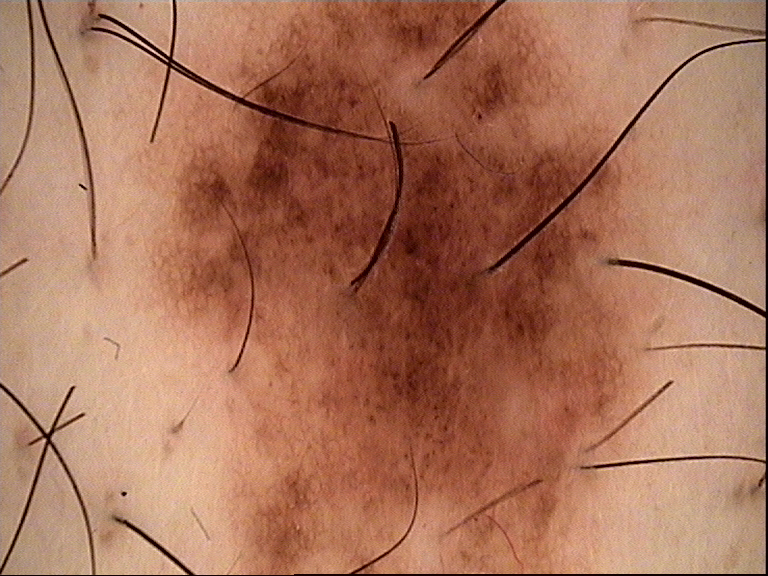diagnostic label = dysplastic compound nevus (expert consensus).